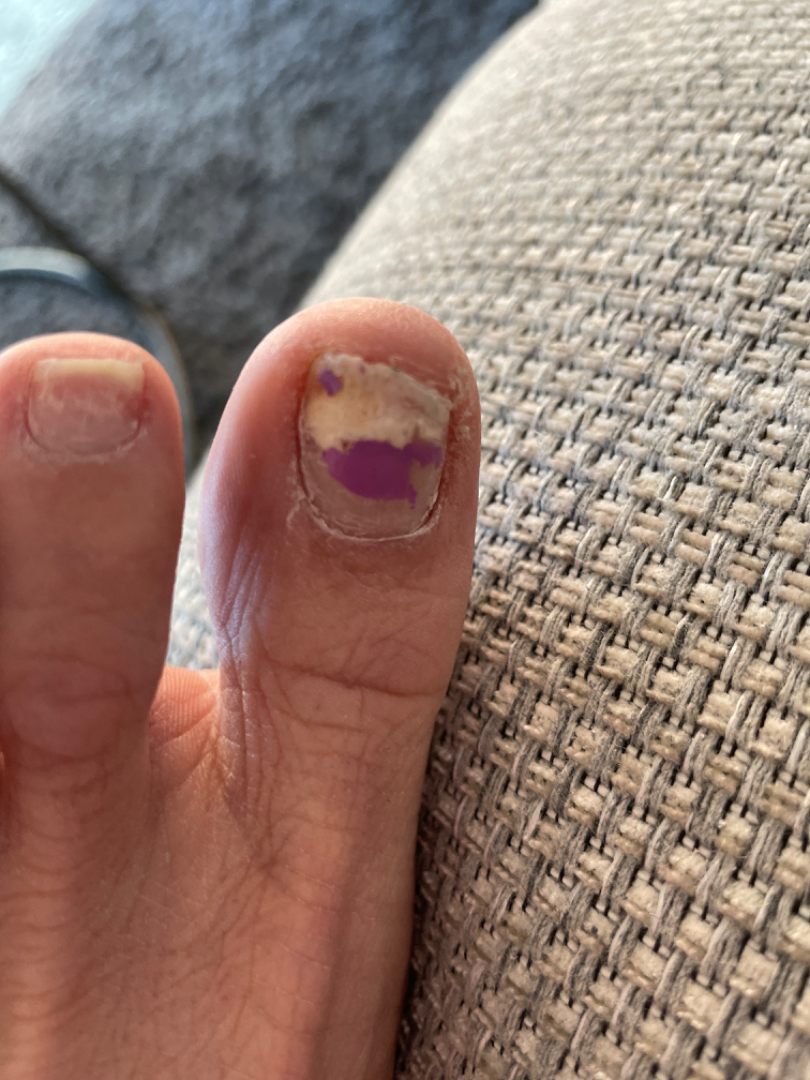One reviewing dermatologist: favoring Onychomycosis; an alternative is Psoriasis.